A male subject roughly 65 years of age; recorded as FST III.
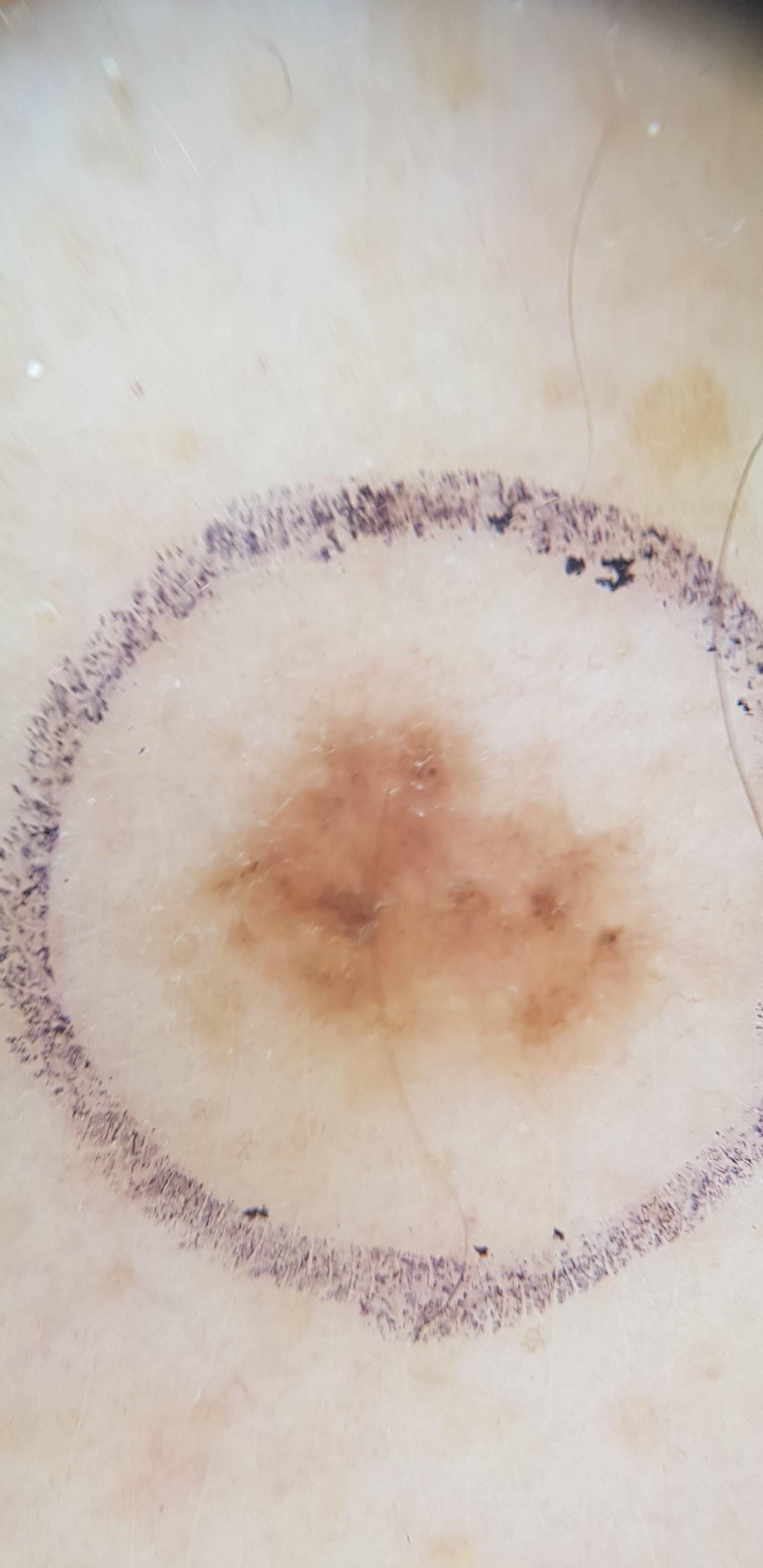location=the posterior trunk
pathology=Basal cell carcinoma (biopsy-proven)